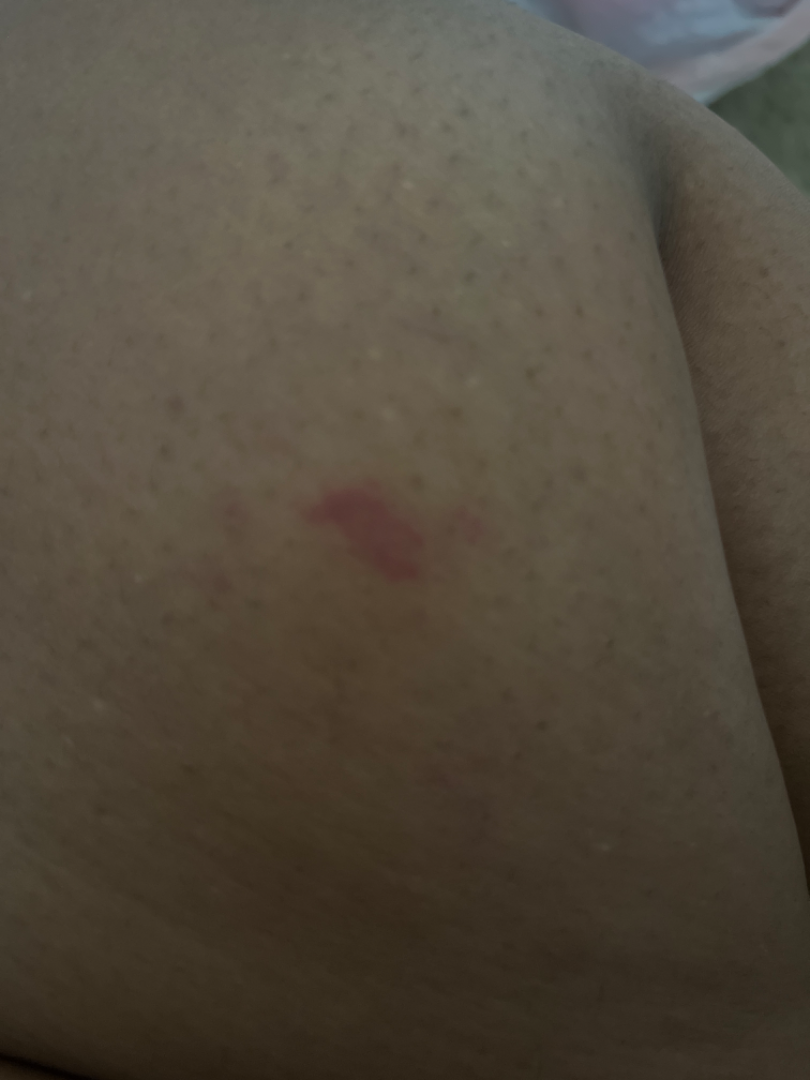Findings:
Diagnostic features were not clearly distinguishable in this photograph.